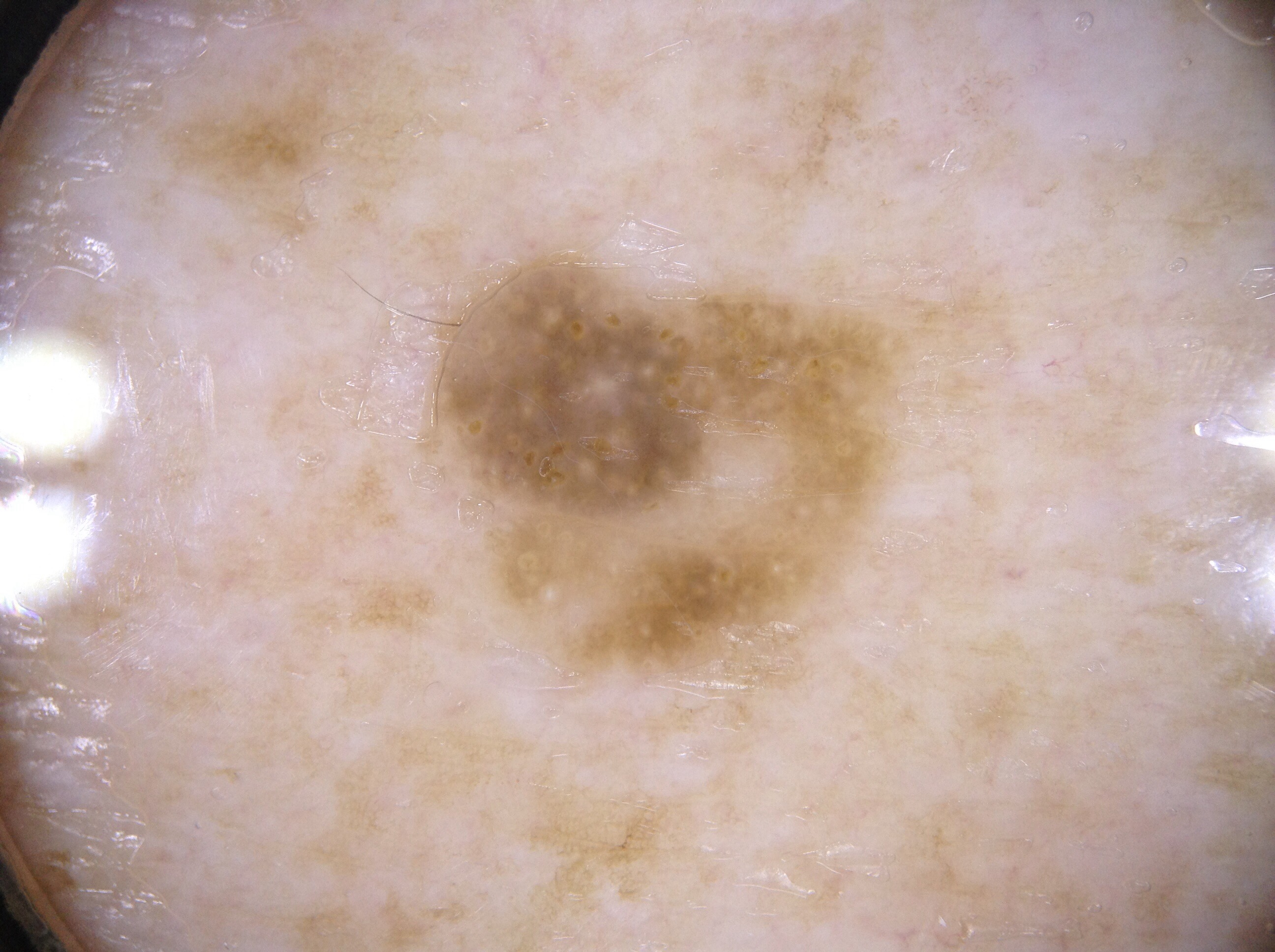The patient is a male aged 68 to 72.
A skin lesion imaged with a dermatoscope.
Dermoscopically, the lesion shows milia-like cysts, with no streaks, pigment network, or negative network.
With coordinates (x1, y1, x2, y2), the lesion is located at box(401, 217, 1019, 738).
Clinically diagnosed as a seborrheic keratosis.